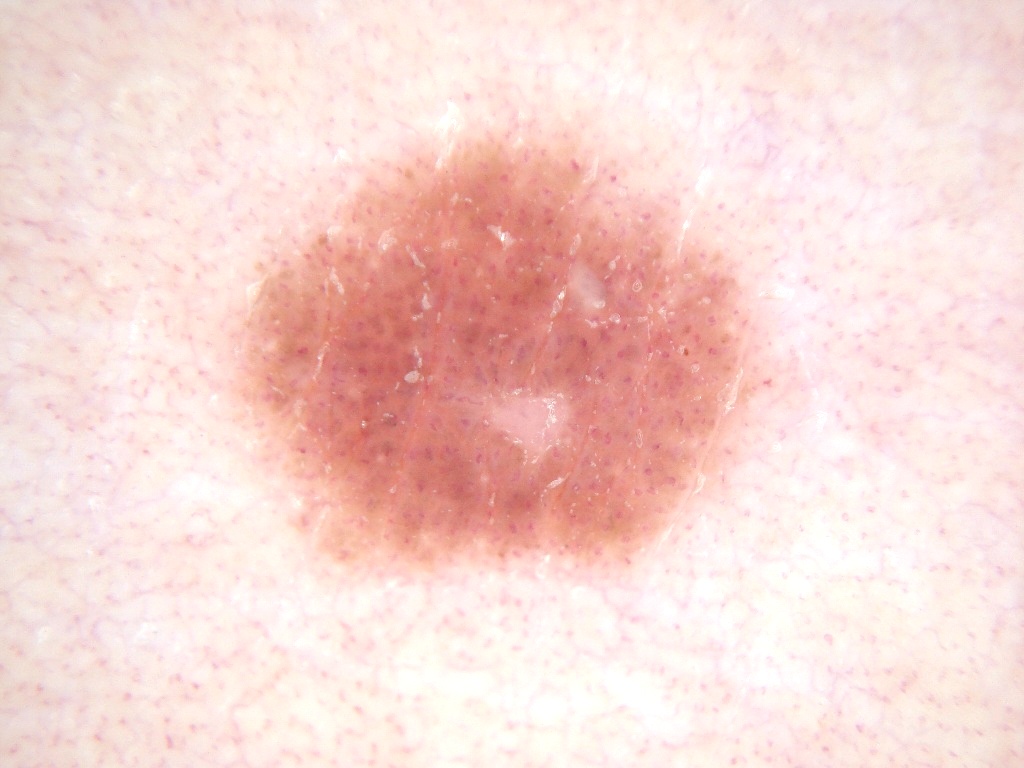Image and clinical context: A dermoscopic image of a skin lesion. A female subject, aged around 25. As (left, top, right, bottom), the visible lesion spans box(209, 116, 784, 582). The dermoscopic pattern shows no negative network, milia-like cysts, pigment network, globules, or streaks. Assessment: Diagnosed as a melanocytic nevus, a benign lesion.